The patient also reports joint pain. The patient described the issue as a rash. Non-clinician graders estimated MST 2 or 3 (two reviewer pools). The contributor notes enlargement, bleeding, darkening, itching, pain, bothersome appearance and burning. Reported duration is less than one week. The contributor notes the lesion is rough or flaky, fluid-filled and raised or bumpy. The photograph was taken at an angle. The lesion involves the arm:
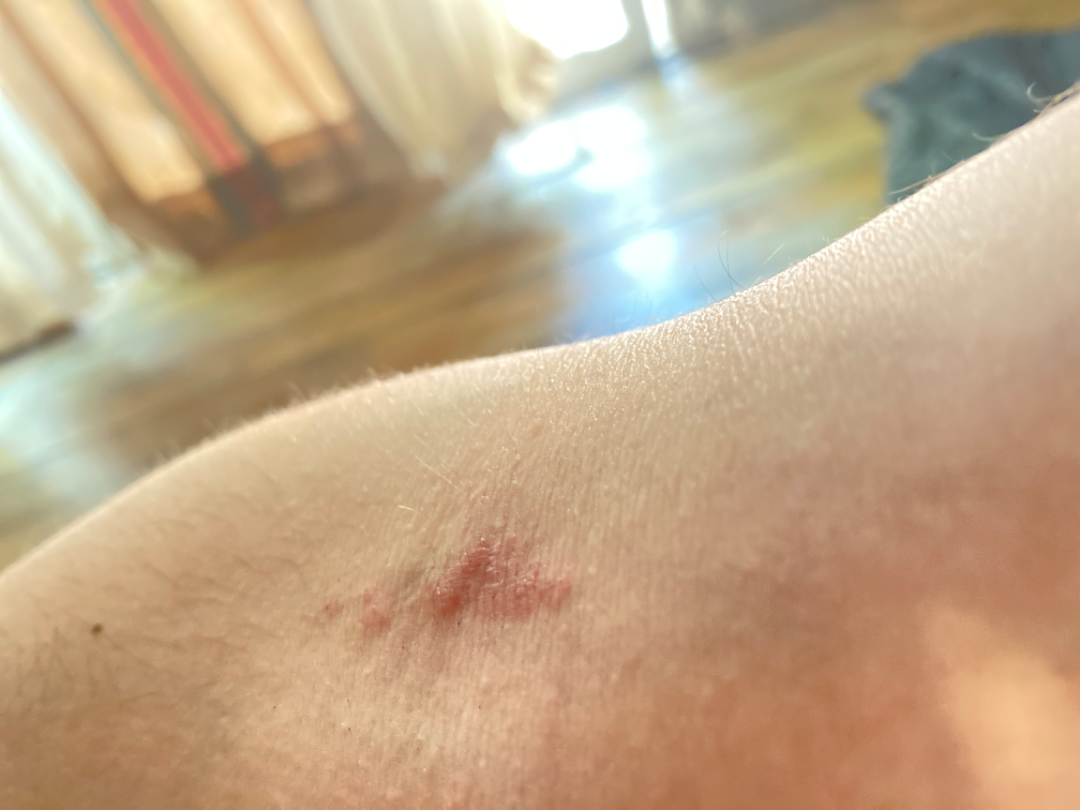diagnostic considerations = pathergy (0.41); Kaposi's sarcoma of skin (0.41); Abrasion, scrape, or scab (0.18).